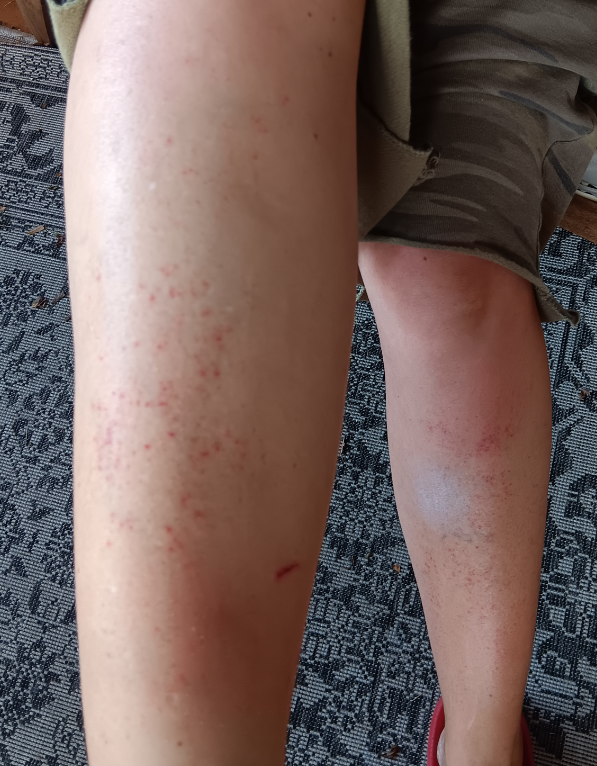| key | value |
|---|---|
| patient-reported symptoms | itching and bothersome appearance |
| associated systemic symptoms | none reported |
| anatomic site | leg |
| self-categorized as | a rash |
| duration | about one day |
| image framing | at a distance |
| texture | flat |
| clinical impression | the differential includes Pigmented purpuric eruption, Eczema and Leukocytoclastic Vasculitis, with no clear leading consideration |